Located on the arm · the subject is a female aged 40–49 · the photograph was taken at a distance — 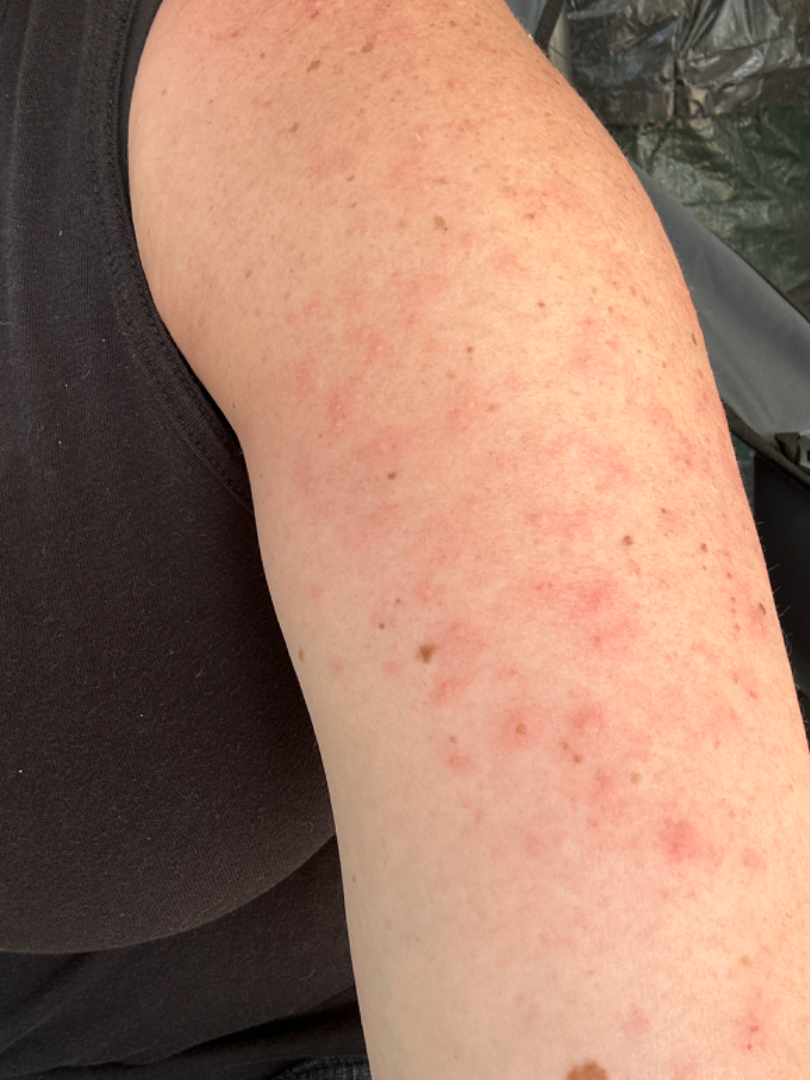The patient indicates the lesion is raised or bumpy and fluid-filled. Symptoms reported: itching, bothersome appearance and pain. The reviewing dermatologists' impression was: most consistent with Acute dermatitis, NOS; less likely is Scabies; lower on the differential is Folliculitis; less probable is Herpes Zoster; a more distant consideration is Drug Rash; a remote consideration is Eczema; less probable is Allergic Contact Dermatitis.